The back of the hand and leg are involved; the photo was captured at an angle; the patient notes enlargement; self-categorized by the patient as a rash; no relevant systemic symptoms; texture is reported as raised or bumpy; present for one to four weeks:
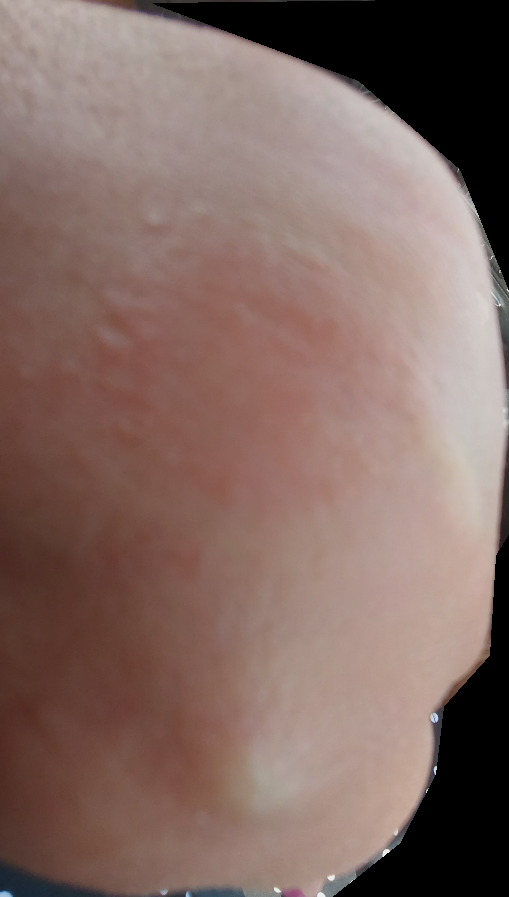diagnostic considerations = most likely Pigmented purpuric eruption; also raised was Tinea; also on the differential is Eczema.